A dermoscopy image of a single skin lesion:
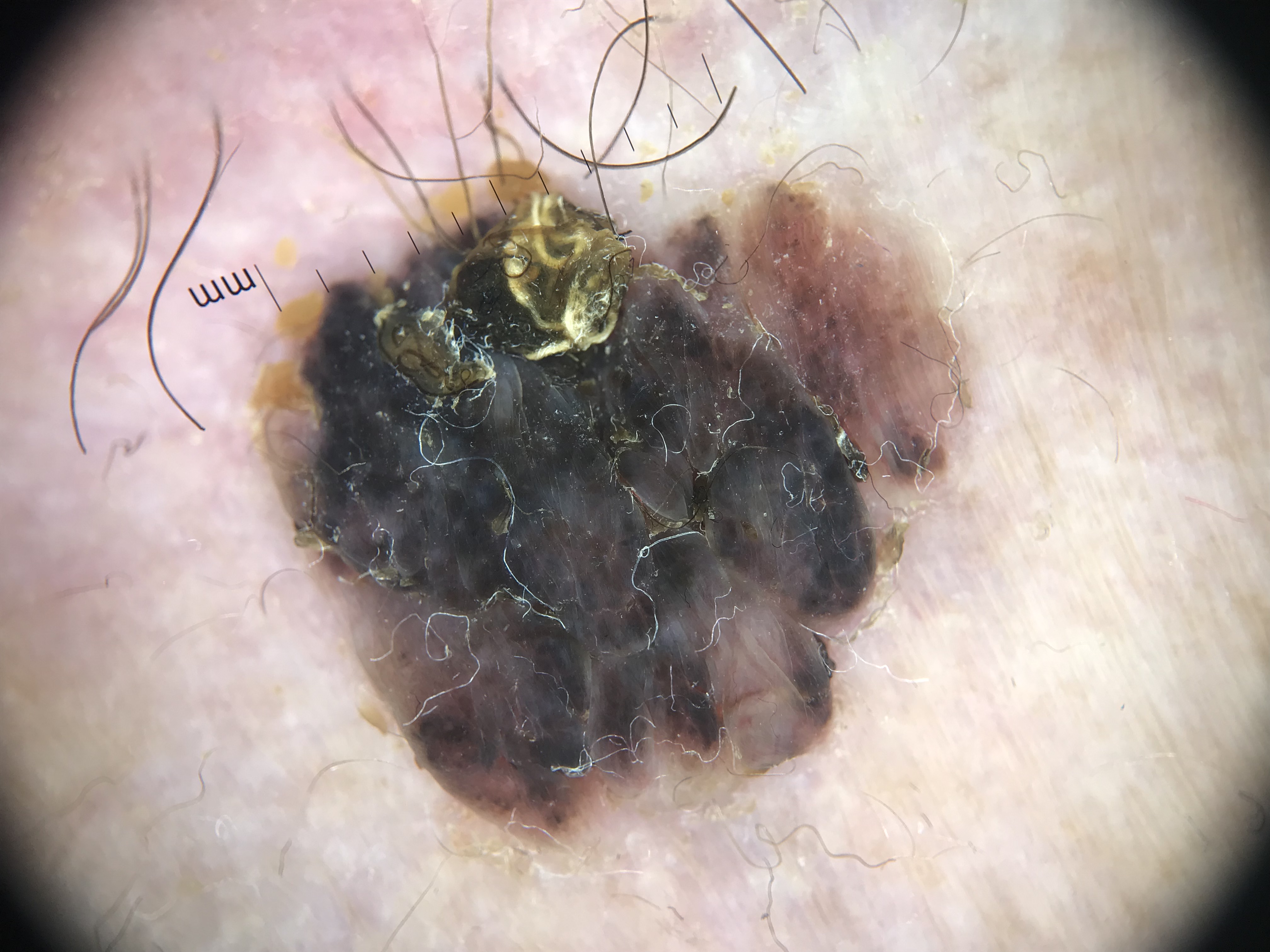| feature | finding |
|---|---|
| class | melanoma (biopsy-proven) |